A macroscopic clinical photograph of a skin lesion · the patient describes having few moles overall: 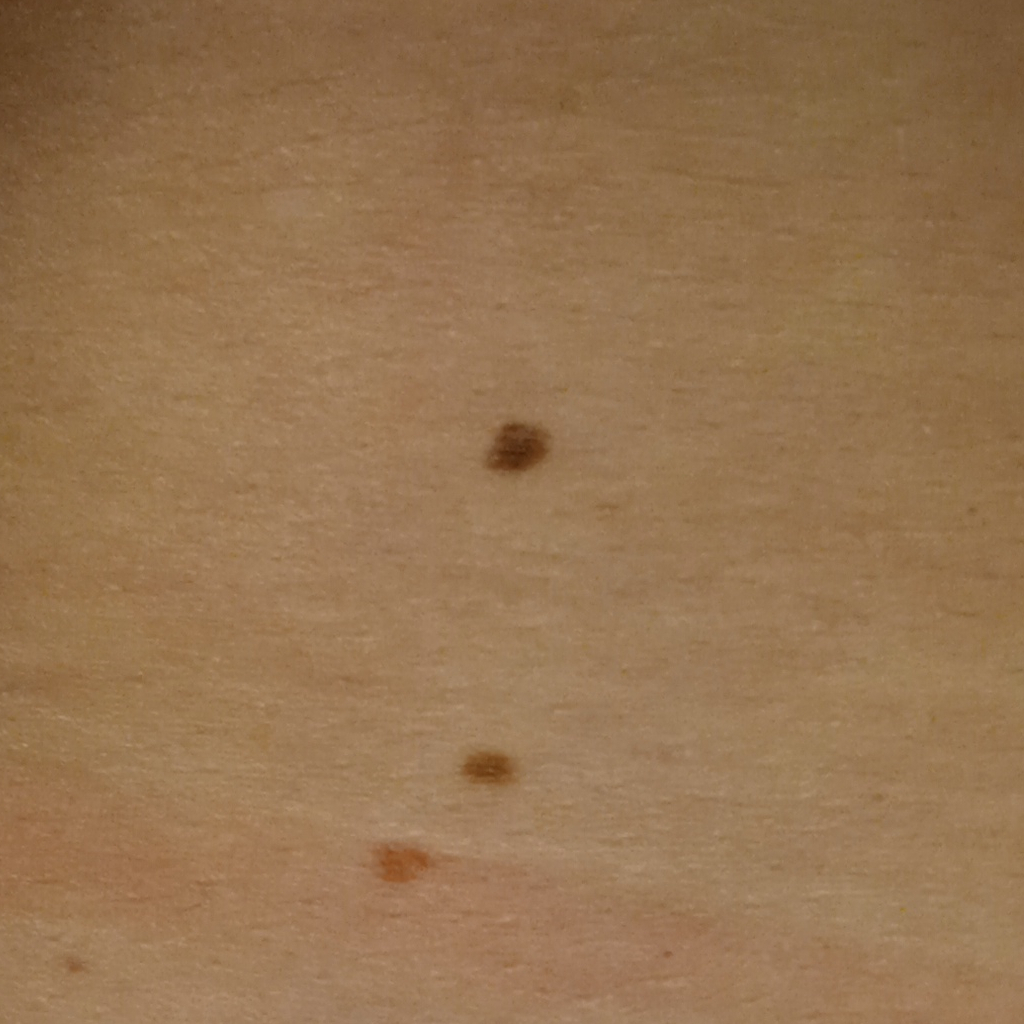The lesion measures approximately 4.3 mm. The lesion was assessed as a melanocytic nevus.